A skin lesion imaged with a dermatoscope.
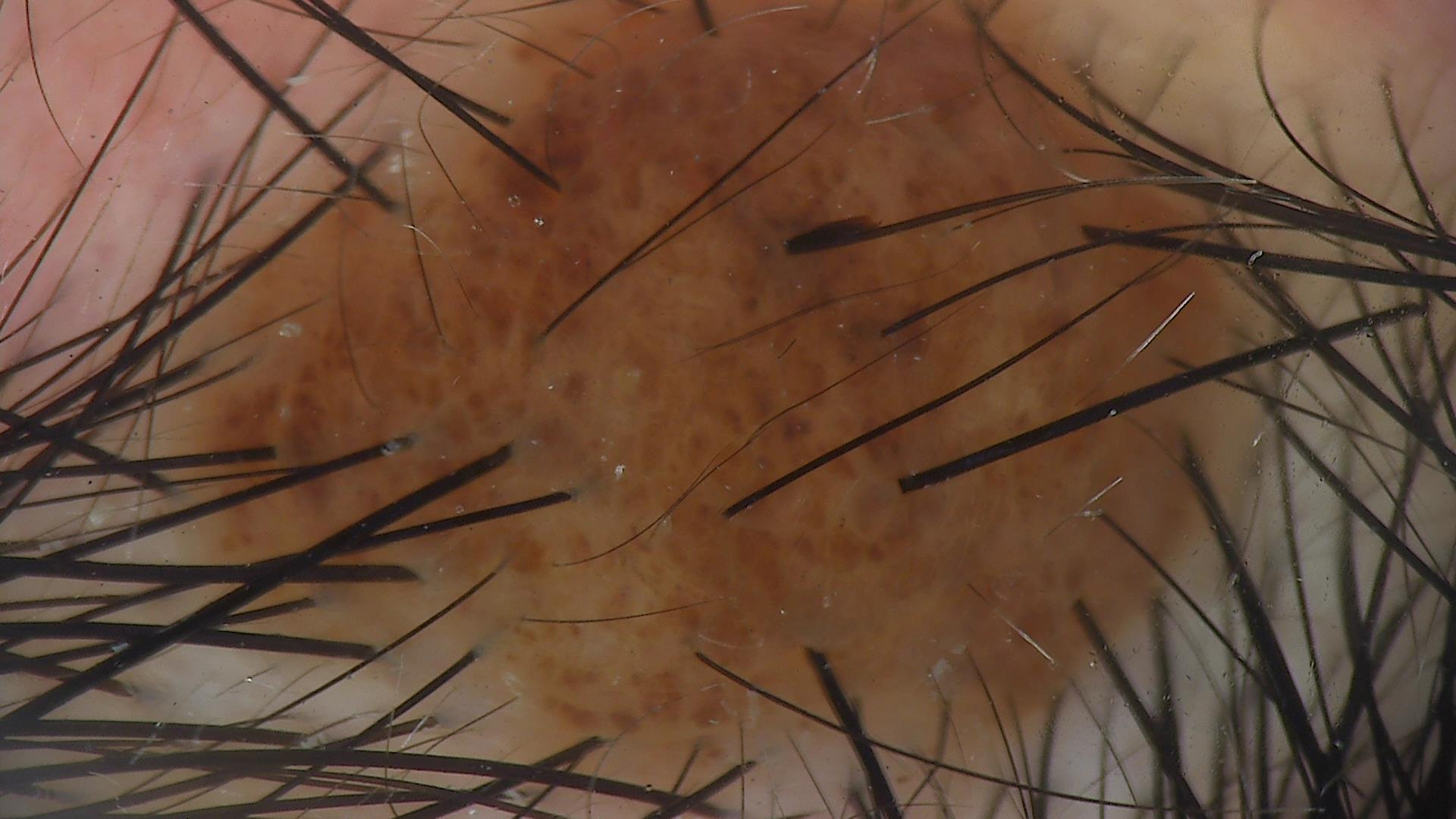Impression:
Labeled as a banal lesion — a congenital compound nevus.